A clinical close-up photograph of a skin lesion · a male subject age 52:
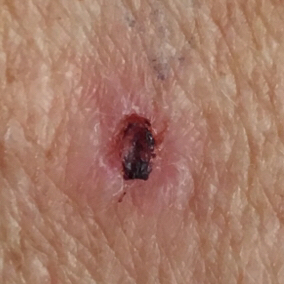- site · the chest
- symptoms · itching, bleeding, elevation
- diagnosis · basal cell carcinoma (biopsy-proven)